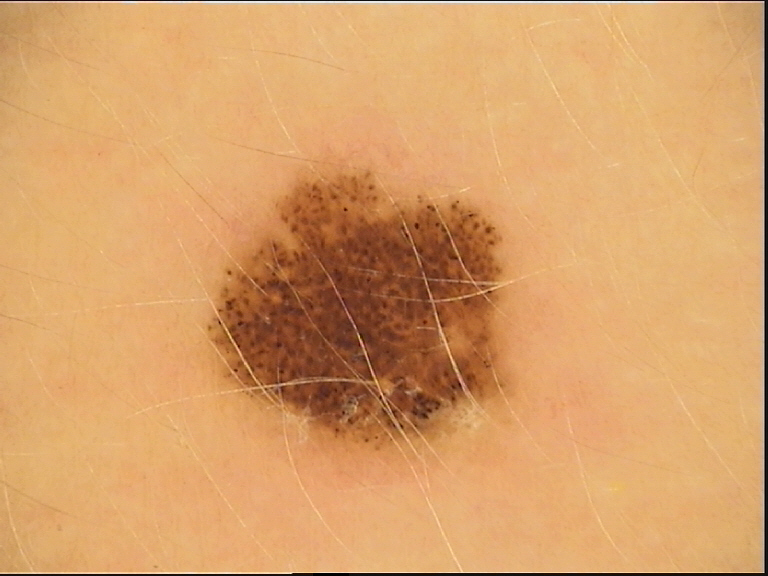assessment: dysplastic junctional nevus (expert consensus).